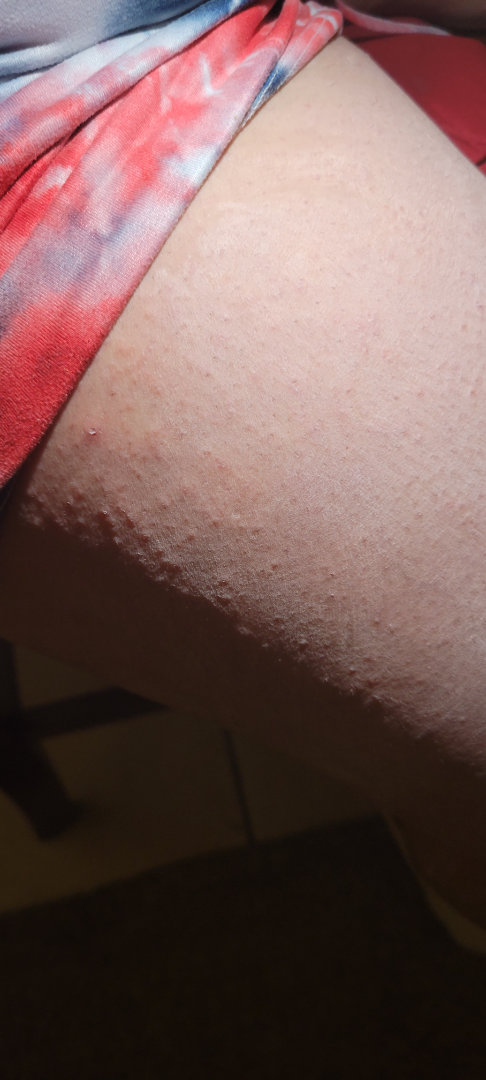{"differential": {"Keratosis pilaris": 0.5, "Eczema": 0.5}}